This is a close-up image · the leg, front of the torso, back of the torso and head or neck are involved.
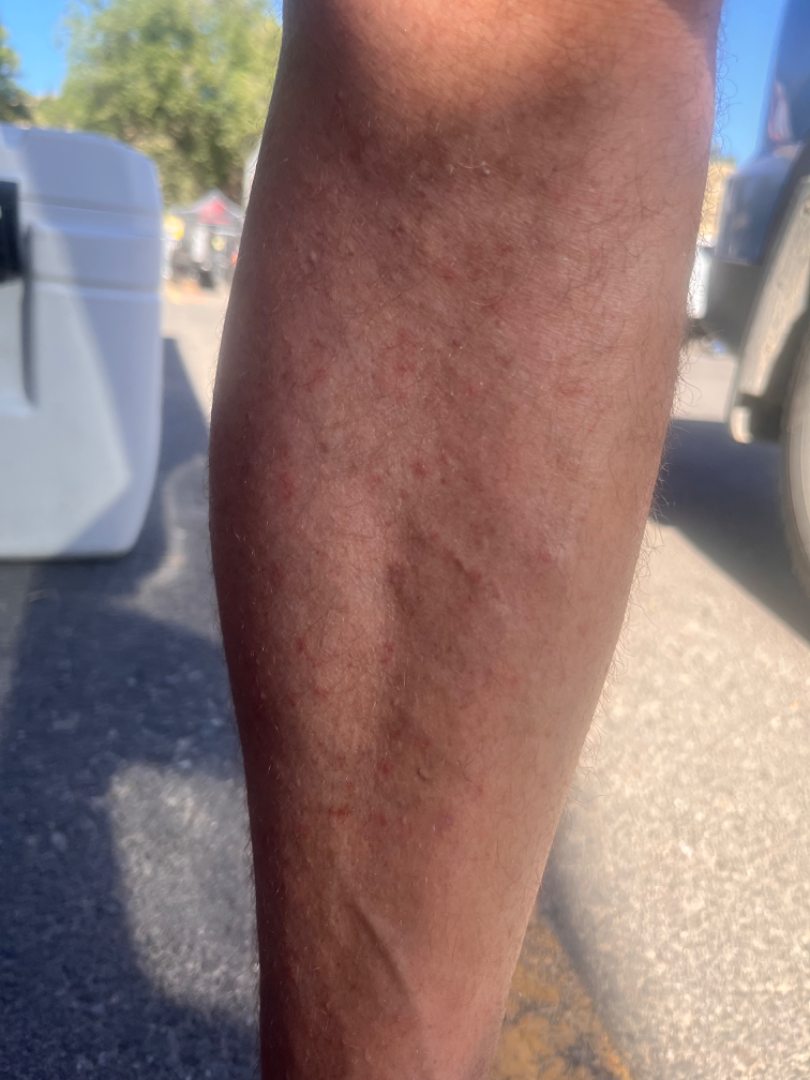The case was difficult to assess from the available photograph.